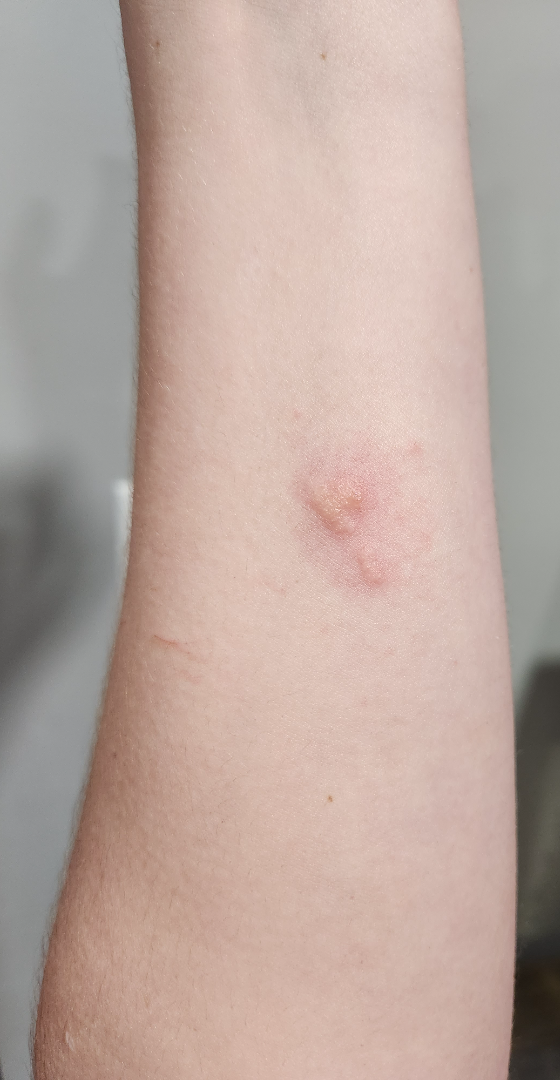On teledermatology review: most consistent with Blister; possibly Herpes Simplex; less probable is Herpes Zoster.